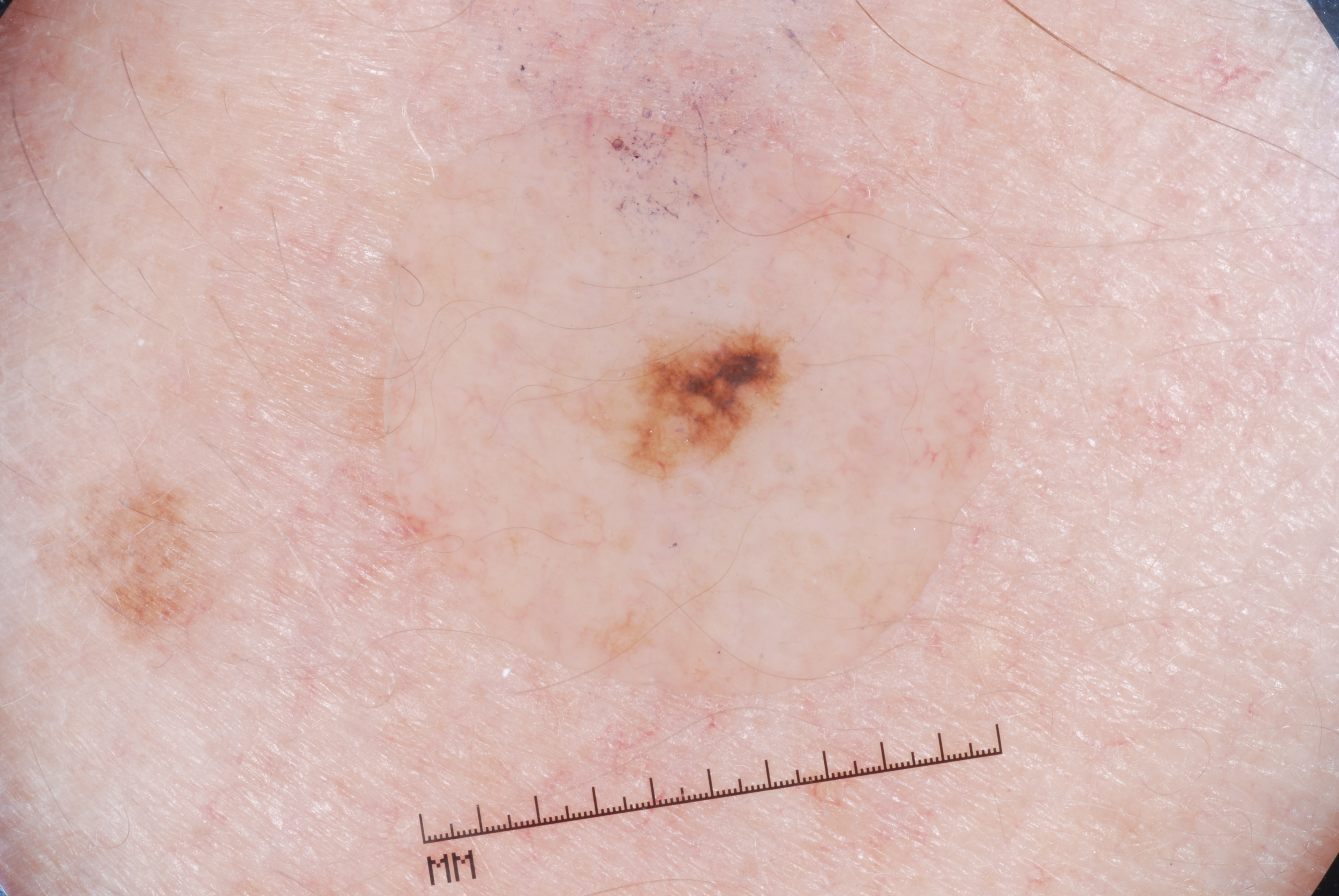A dermoscopic image of a skin lesion. A female subject, aged around 45. The dermoscopic pattern shows milia-like cysts and pigment network. The lesion occupies roughly 2% of the field. As (left, top, right, bottom), the lesion is bounded by 607/322/795/476. The clinical diagnosis was a melanocytic nevus, a benign lesion.